A dermoscopy image of a single skin lesion: 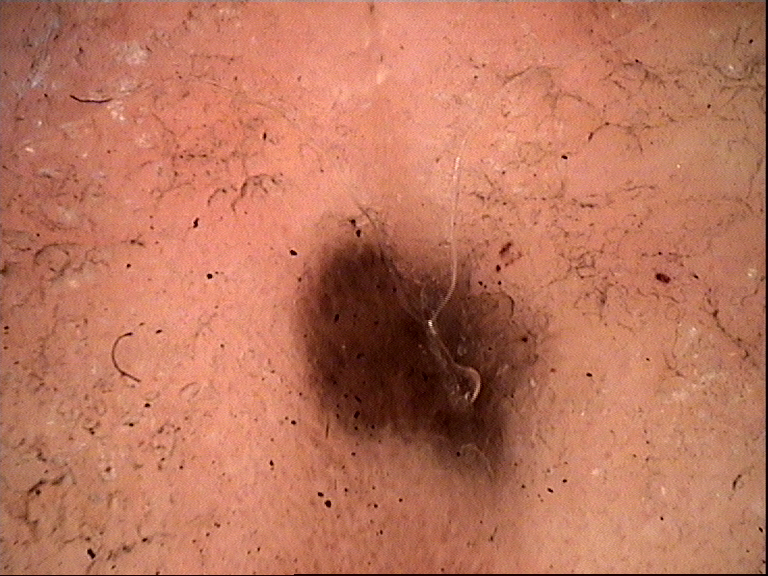The diagnostic label was a benign lesion — an acral dysplastic junctional nevus.